Reported duration is less than one week, the photograph is a close-up of the affected area, the lesion involves the back of the torso and head or neck, no associated systemic symptoms reported.
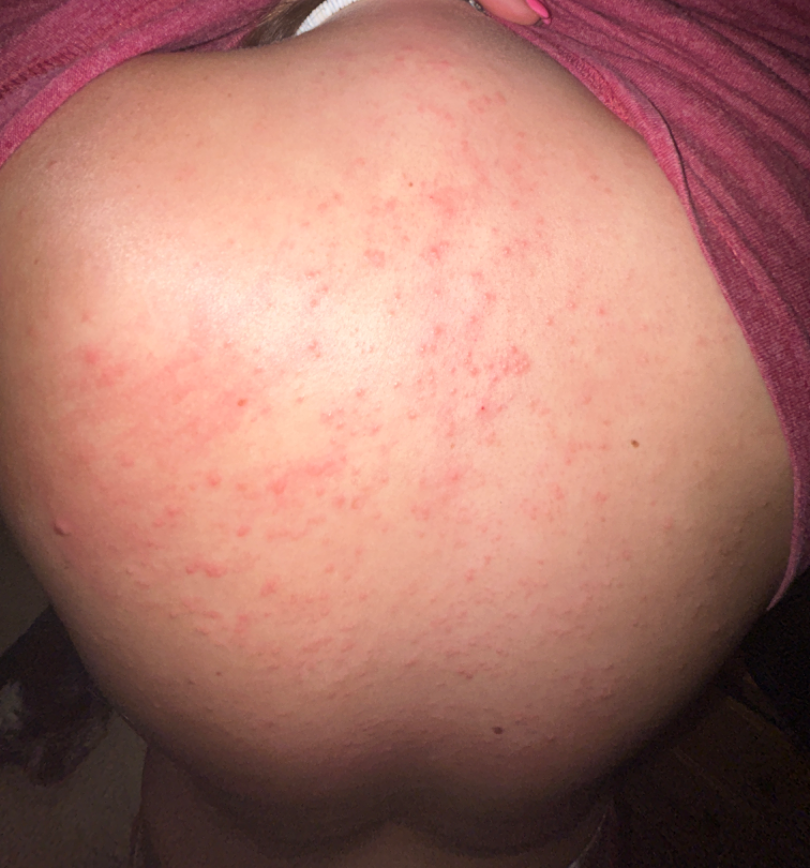The leading impression is Folliculitis; the differential also includes Acne.